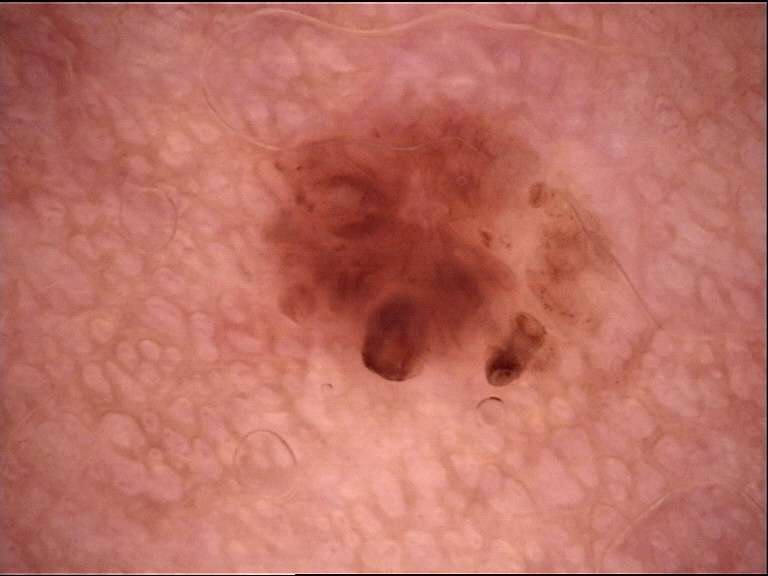* diagnosis — dermal nevus (expert consensus)